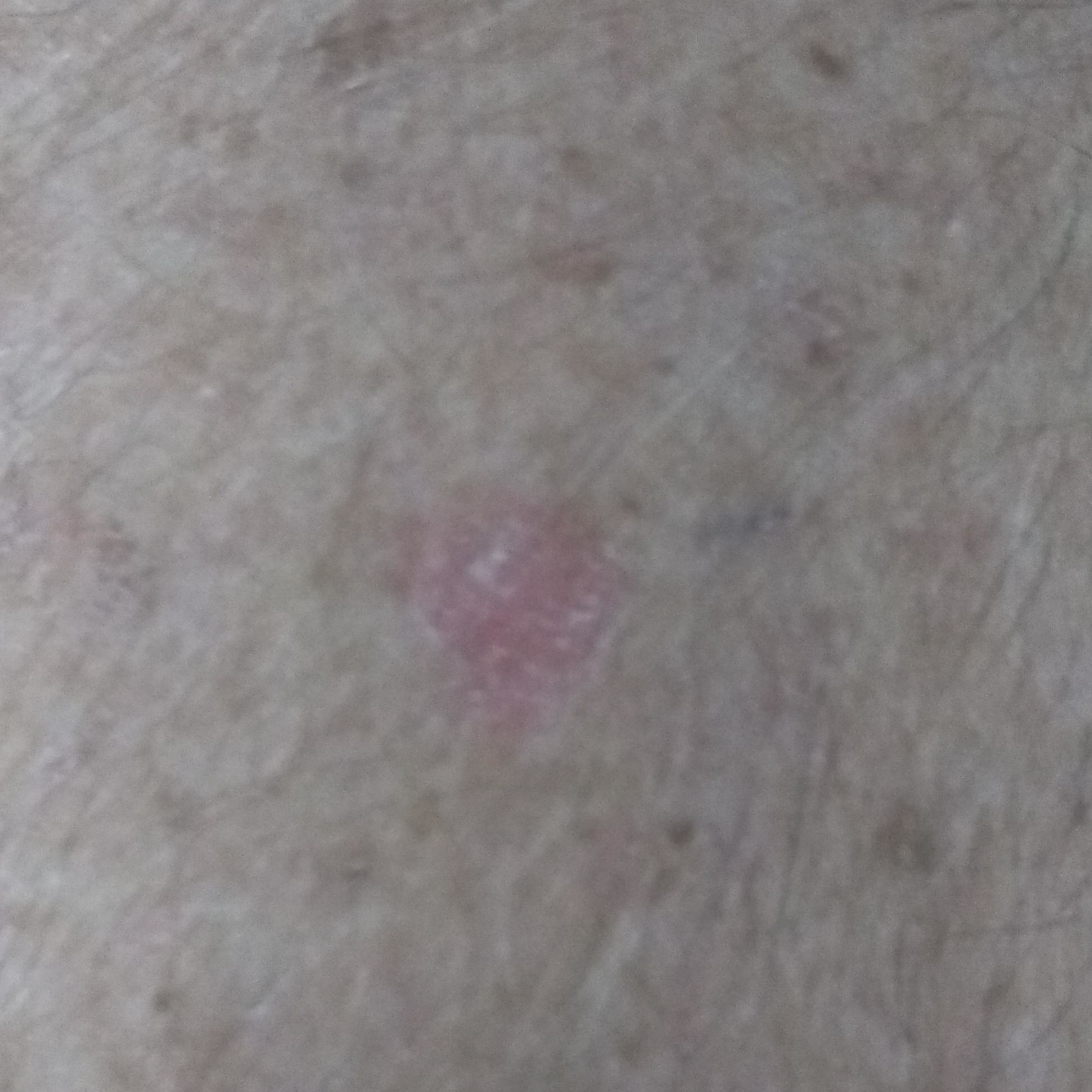Summary:
A clinical photo of a skin lesion taken with a smartphone. The lesion is on a forearm. By the patient's account, the lesion itches, but has not bled.
Impression:
Clinically diagnosed as an actinic keratosis.